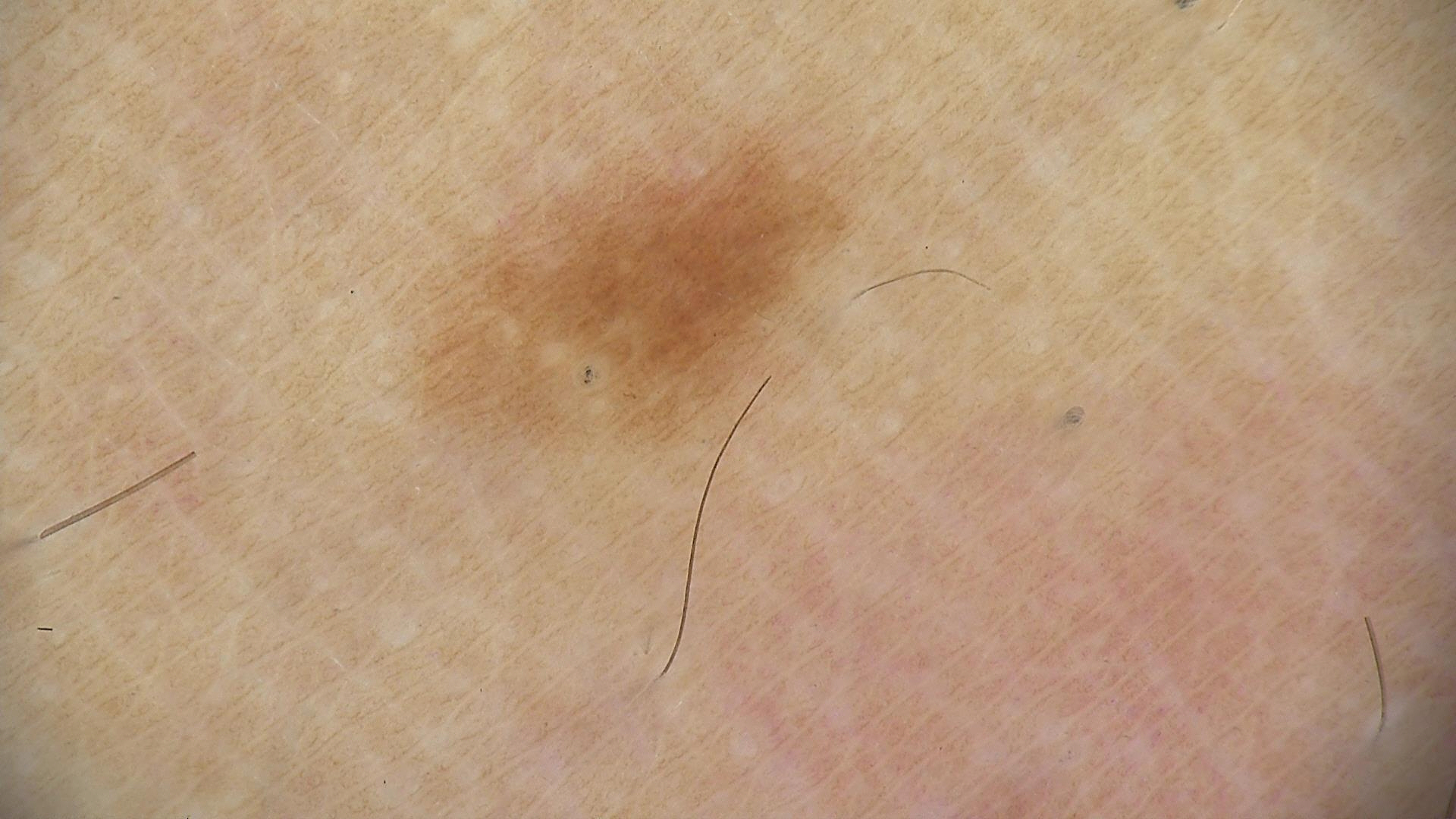modality = dermoscopy, assessment = dysplastic junctional nevus (expert consensus).